A dermoscopy image of a single skin lesion.
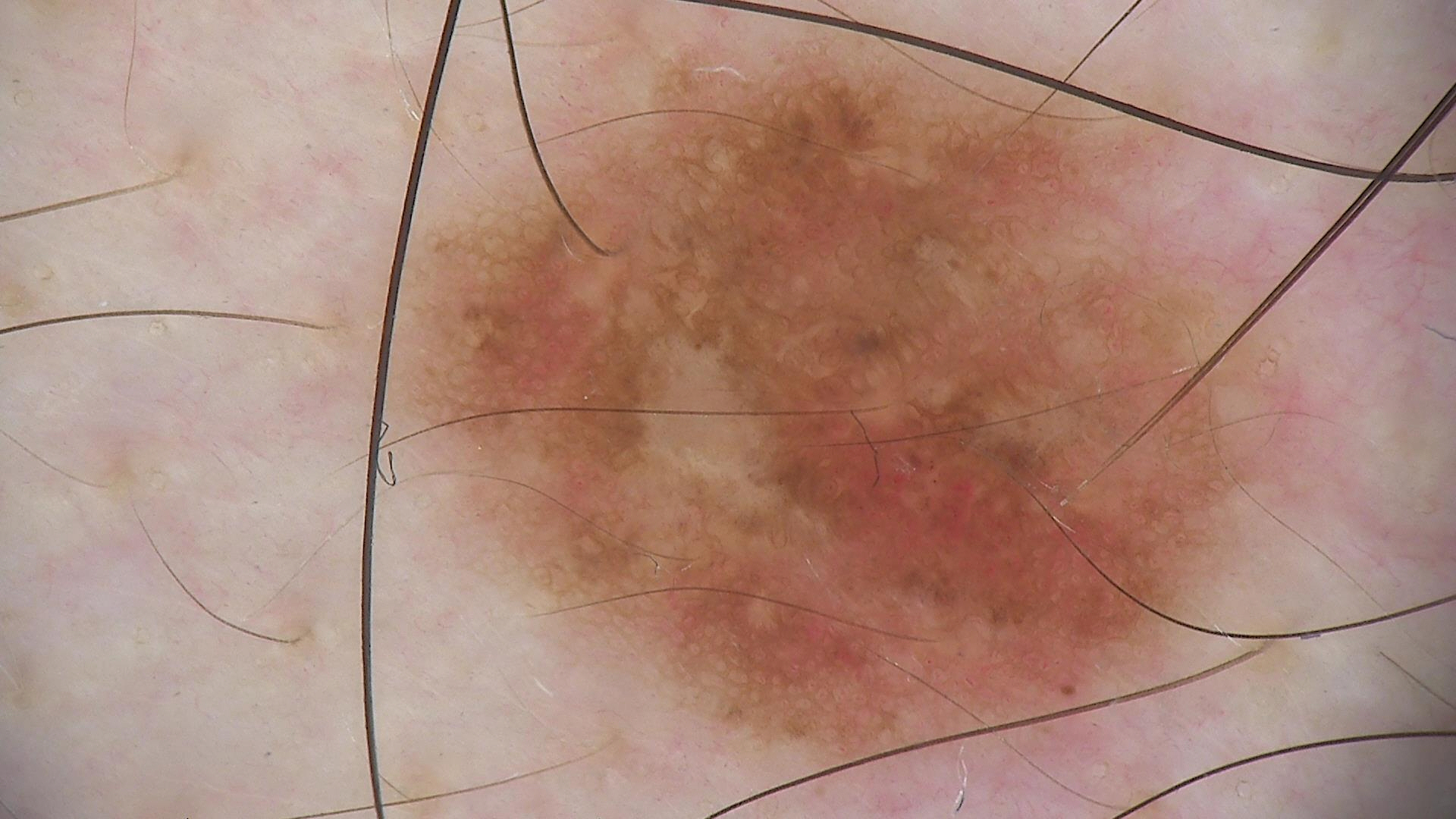The diagnosis was a dysplastic compound nevus.